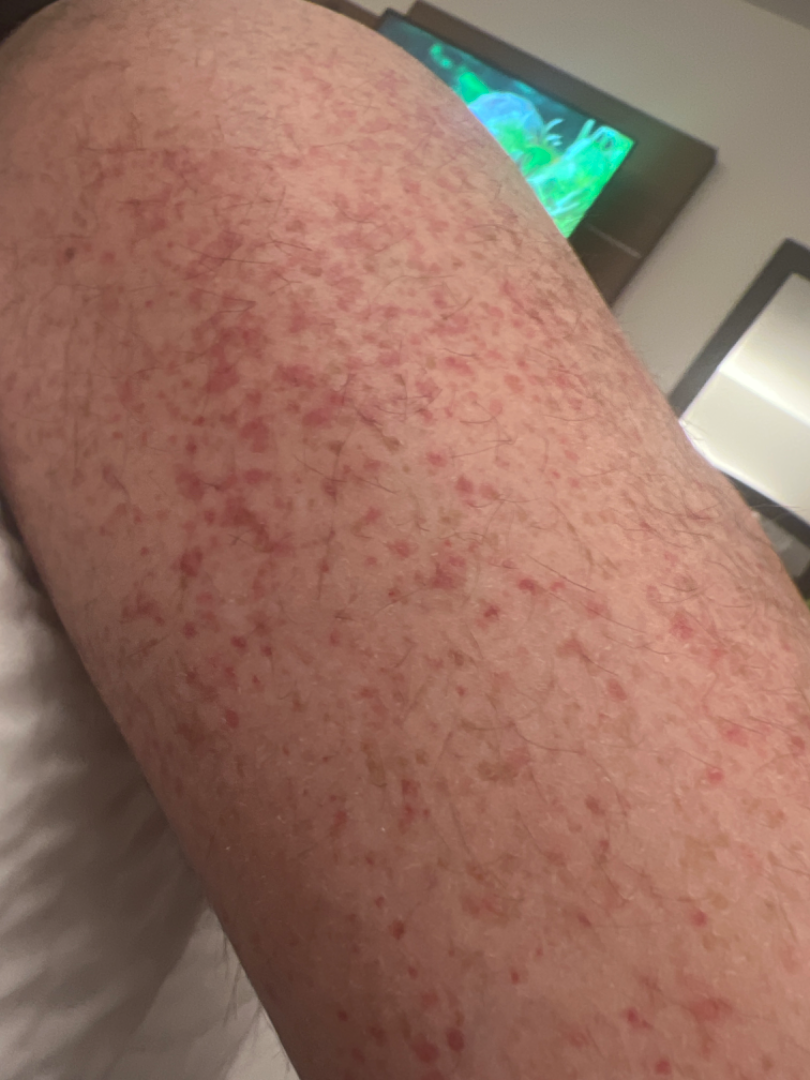The photograph was taken at an angle. The lesion involves the leg. On dermatologist assessment of the image: the impression is Leukocytoclastic Vasculitis.